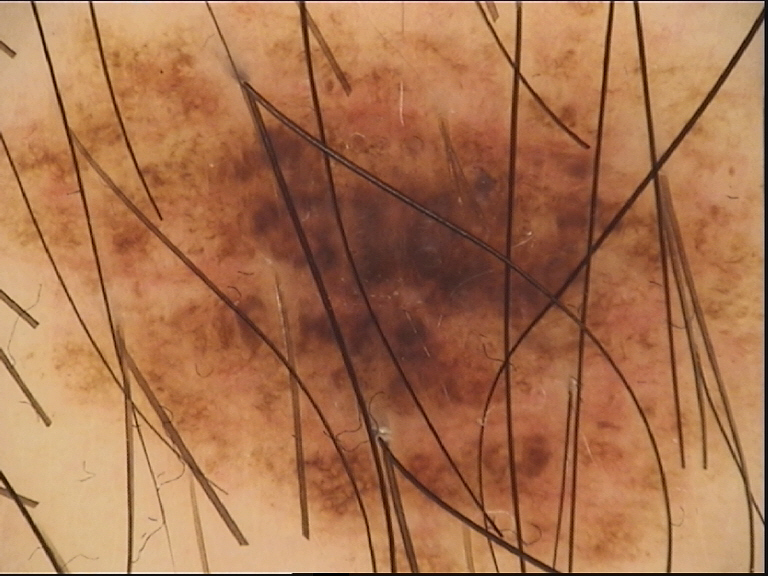  image: dermatoscopy
  diagnosis:
    name: dysplastic compound nevus
    code: cd
    malignancy: benign
    super_class: melanocytic
    confirmation: expert consensus